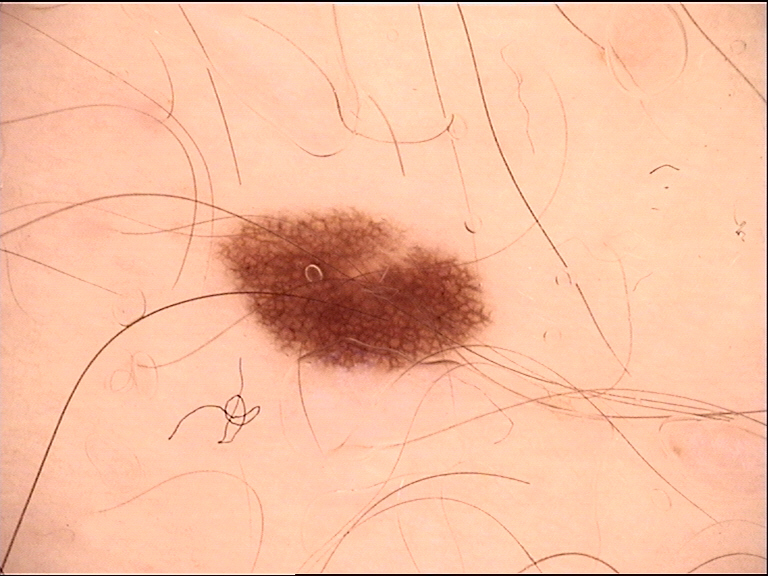Classified as a junctional nevus.